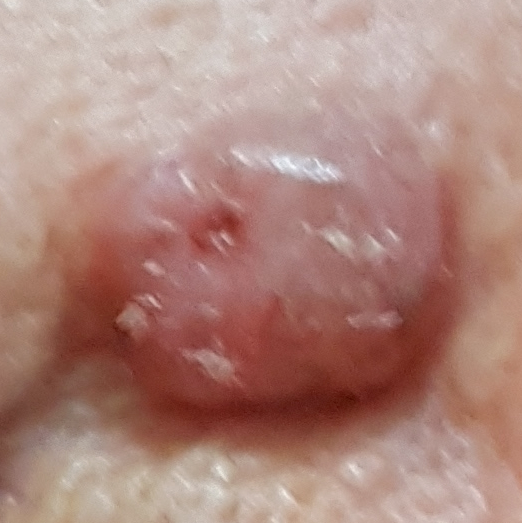Diagnosis:
Histopathology confirmed a basal cell carcinoma.